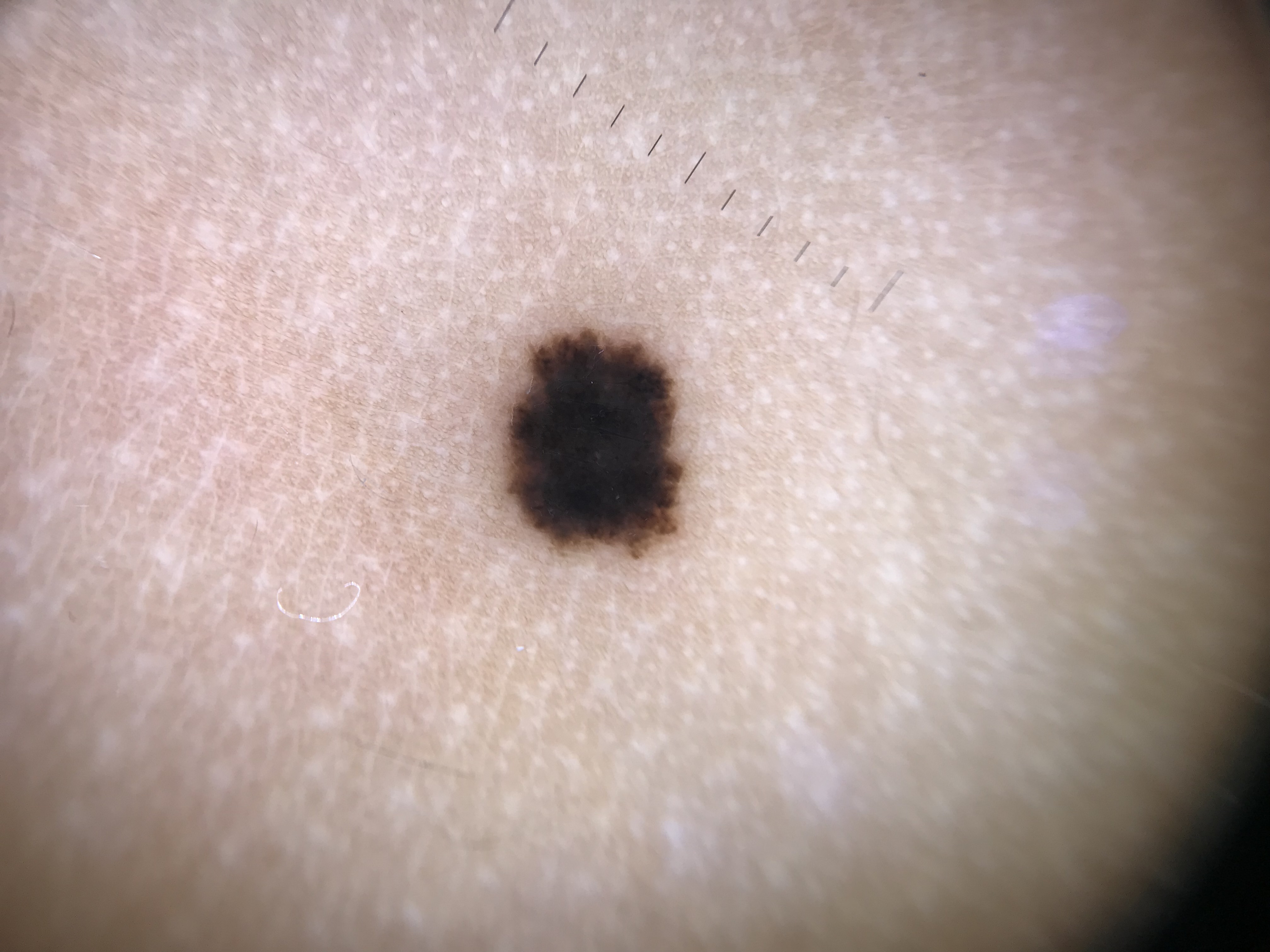Findings:
* diagnostic label: Spitz/Reed nevus (expert consensus)